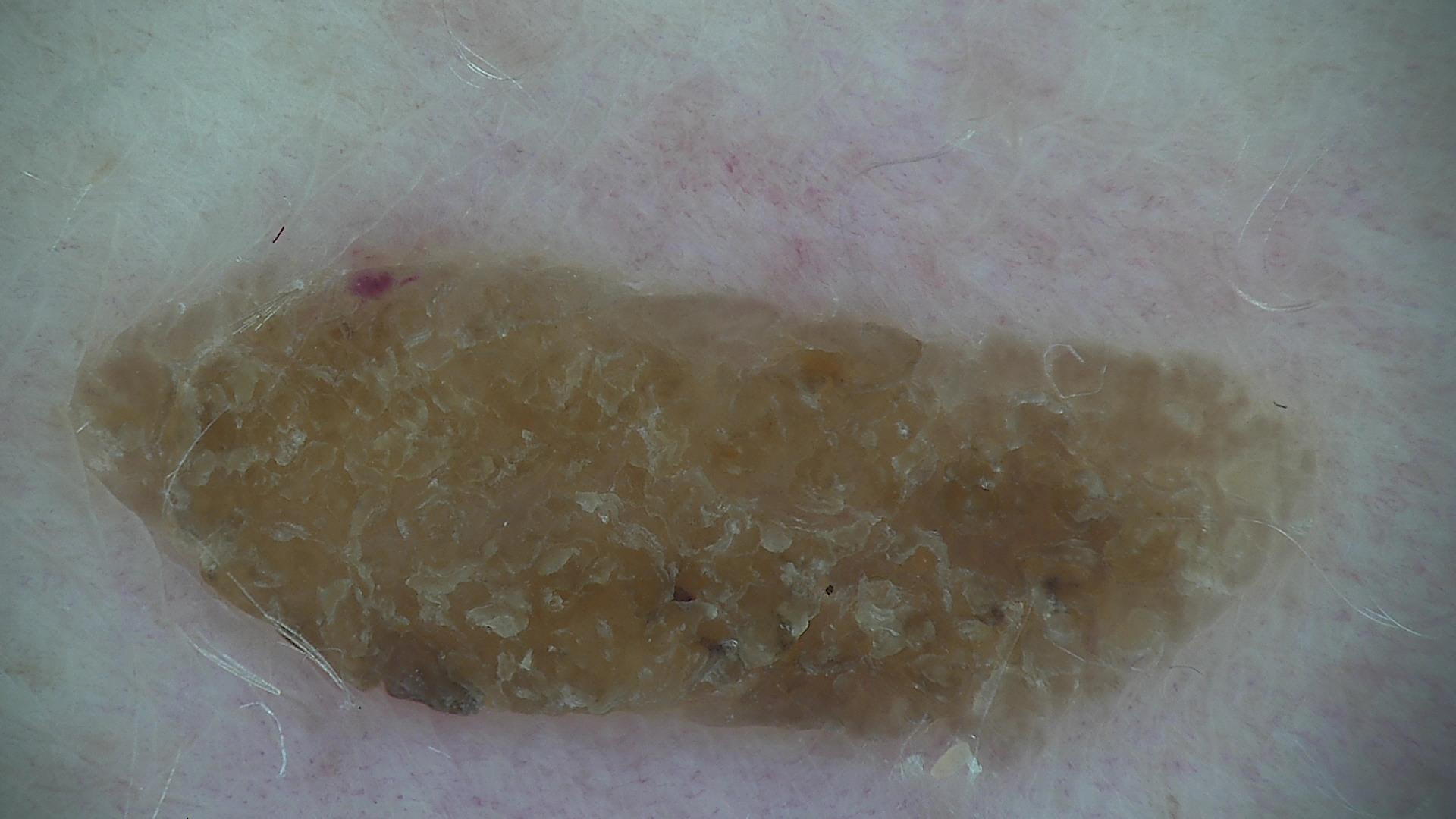modality — dermatoscopy | assessment — seborrheic keratosis (expert consensus).